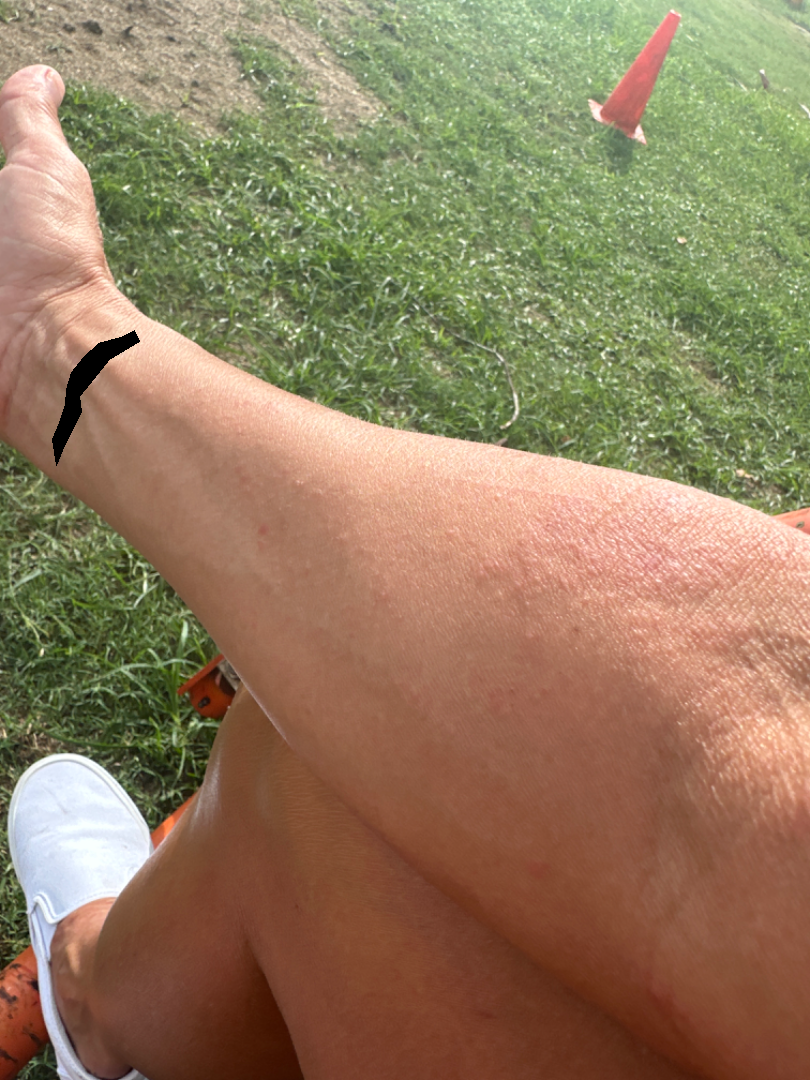described texture = raised or bumpy
patient's own categorization = a rash
image framing = at an angle
present for = one to four weeks
symptoms = burning, enlargement and itching
location = arm
differential = Eczema (favored); Allergic Contact Dermatitis (possible)